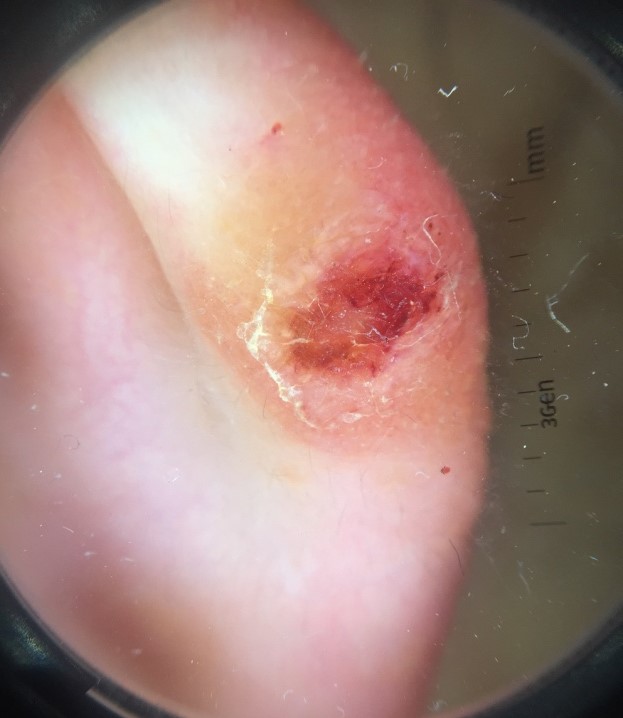Diagnosis: Confirmed on histopathology as a squamous cell carcinoma.